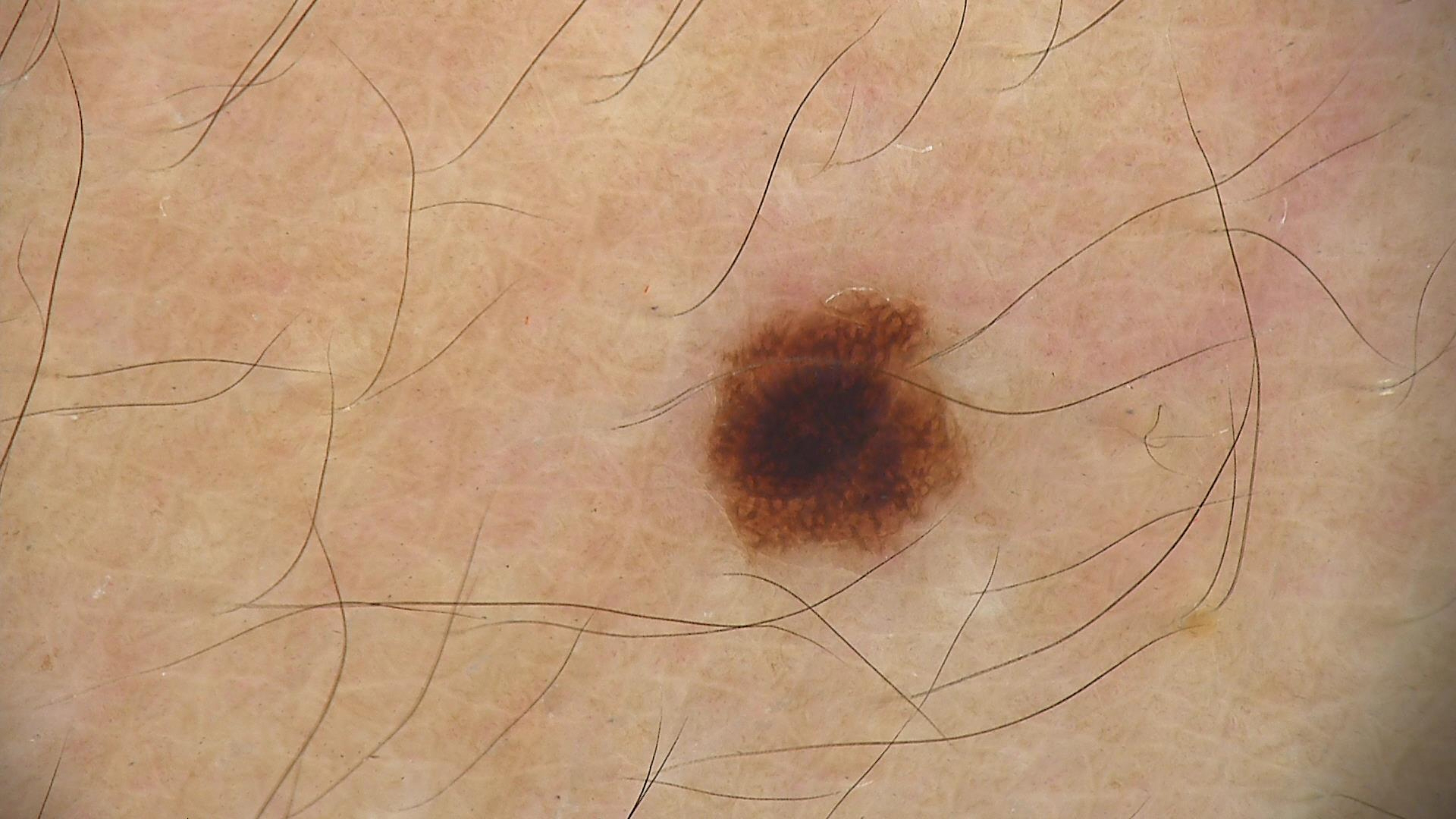class: dysplastic junctional nevus (expert consensus).